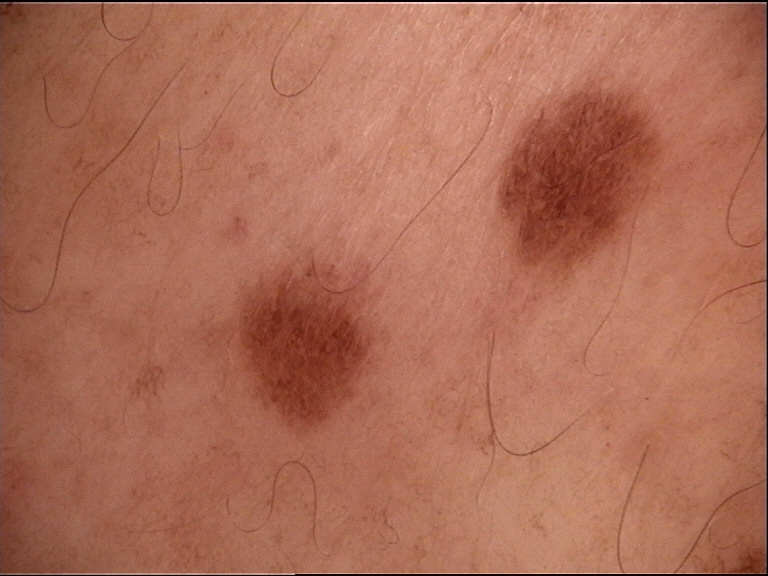{
  "diagnosis": {
    "name": "dysplastic junctional nevus",
    "code": "jd",
    "malignancy": "benign",
    "super_class": "melanocytic",
    "confirmation": "expert consensus"
  }
}